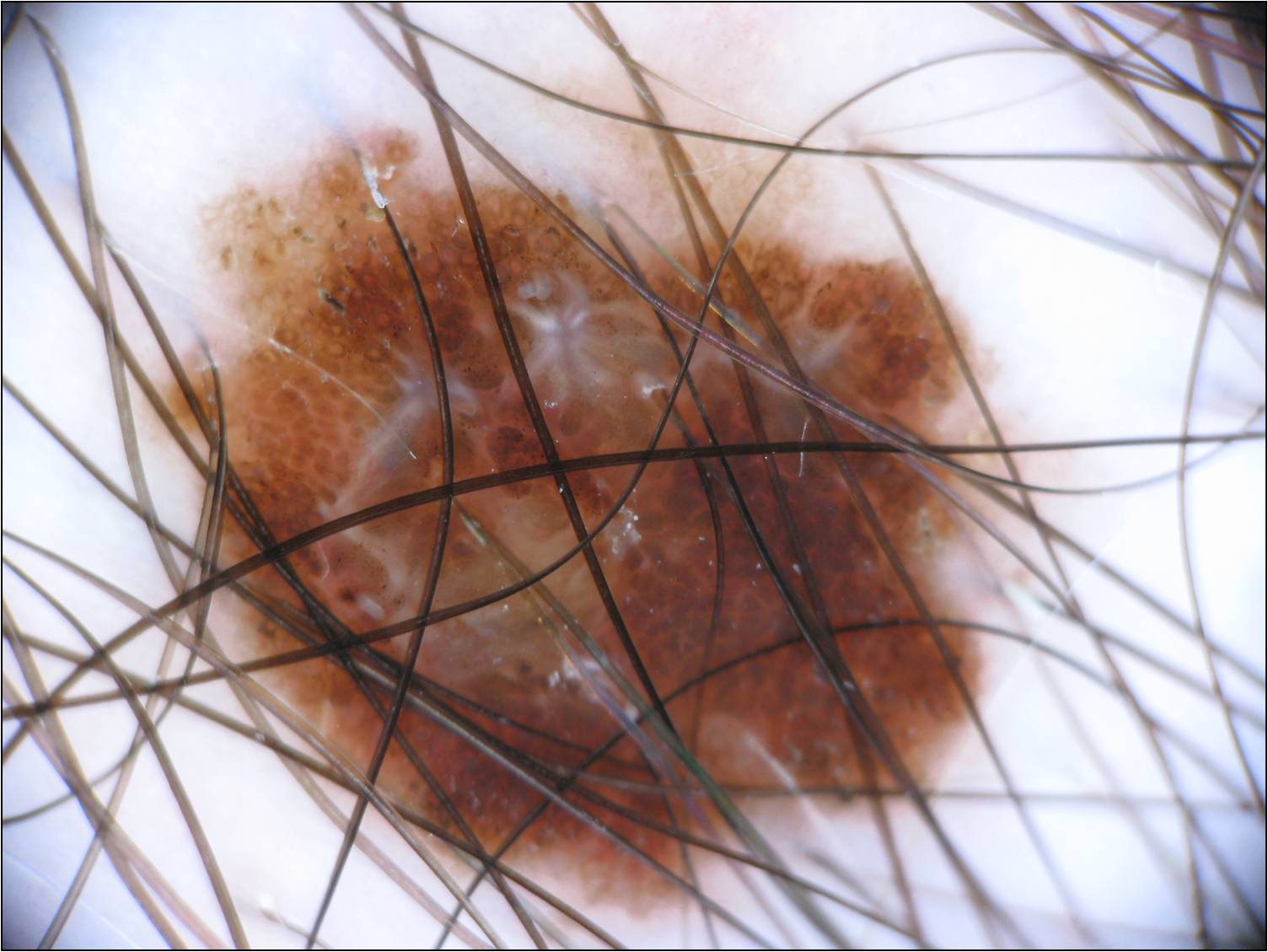A dermatoscopic image of a skin lesion.
The patient is a male aged approximately 35.
As (left, top, right, bottom), the lesion occupies the region box(165, 121, 1031, 918).
Dermoscopy demonstrates globules, negative network, and pigment network, with no milia-like cysts or streaks.
Histopathologically confirmed as a melanoma, a malignancy.